A female subject age 55 — 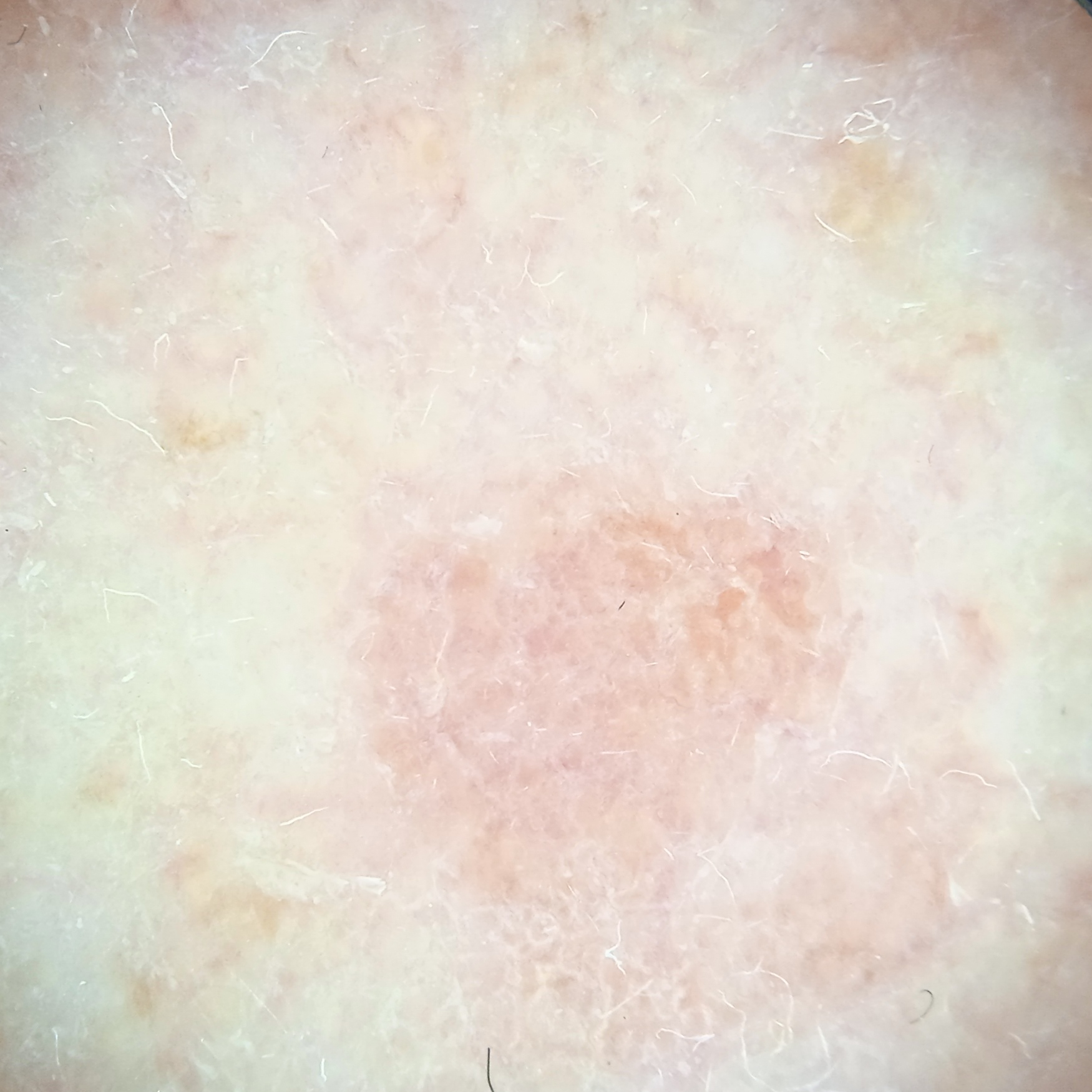Clinical context: The lesion is on the face. The lesion is about 5.7 mm across. Conclusion: The consensus diagnosis for this lesion was an actinic keratosis.